A dermoscopic image of a skin lesion.
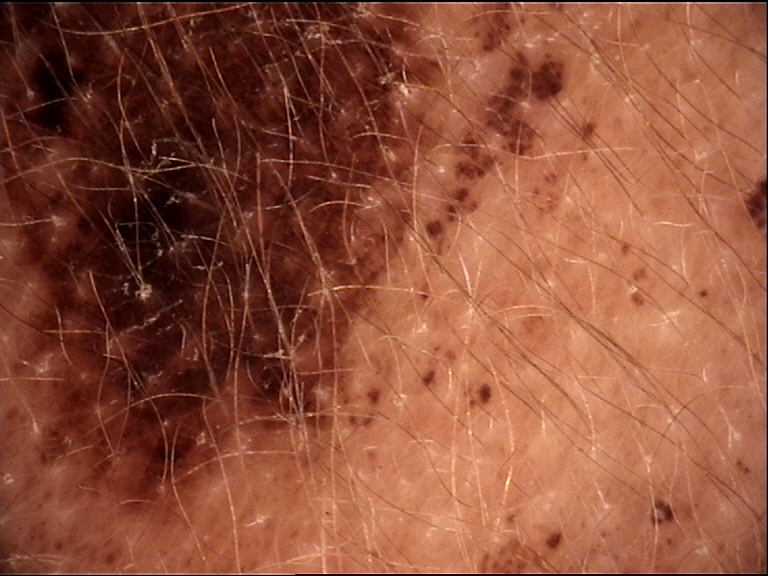Conclusion: Consistent with a congenital compound nevus.